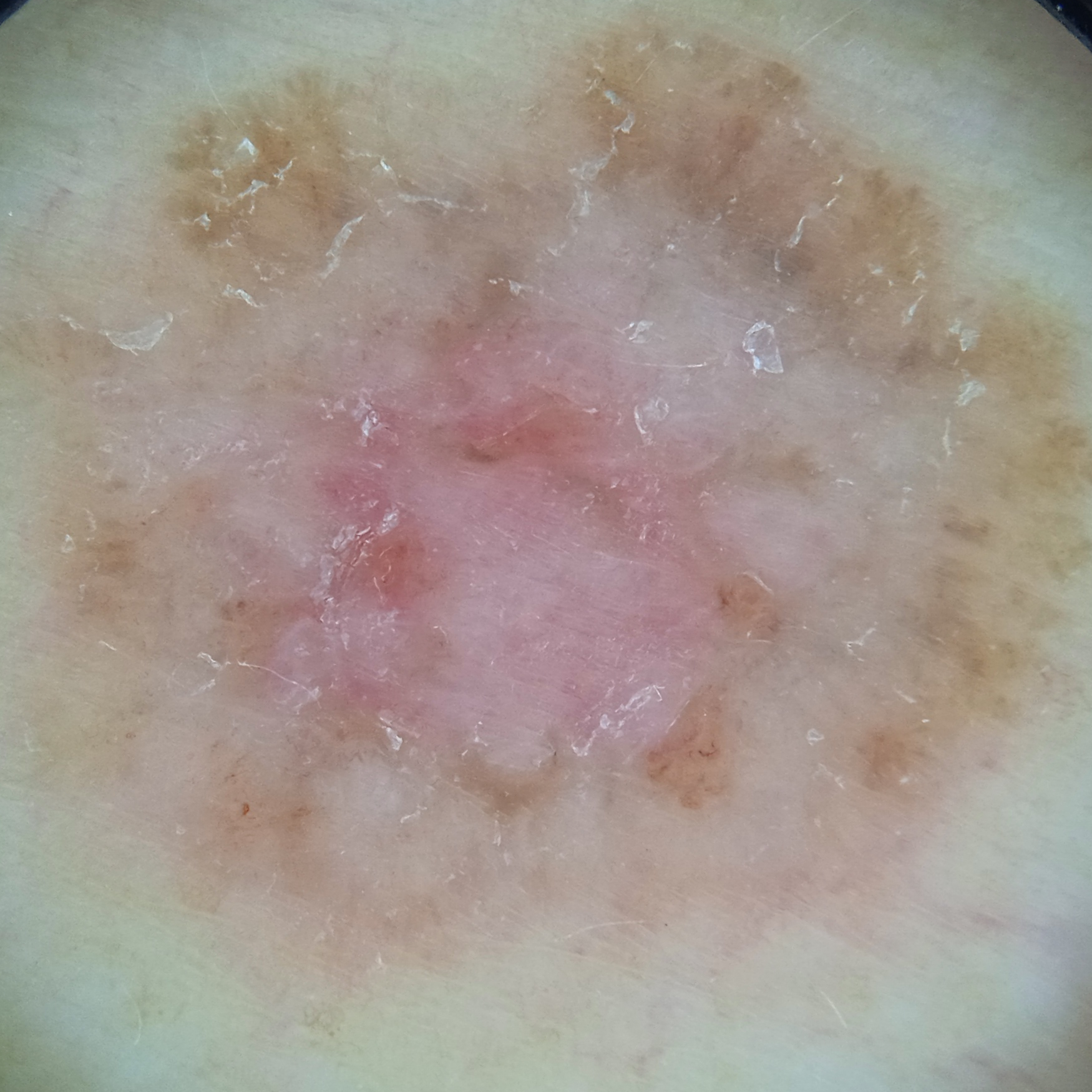{"image": "dermatoscopic image", "patient": {"age": 60, "sex": "female"}, "risk_factors": {"positive": ["a personal history of skin cancer", "a personal history of cancer"]}, "sun_reaction": "skin tans without first burning", "mole_burden": "few melanocytic nevi overall", "lesion_location": "the torso", "lesion_size": {"diameter_mm": 13.2}, "diagnosis": {"name": "basal cell carcinoma", "malignancy": "malignant"}}